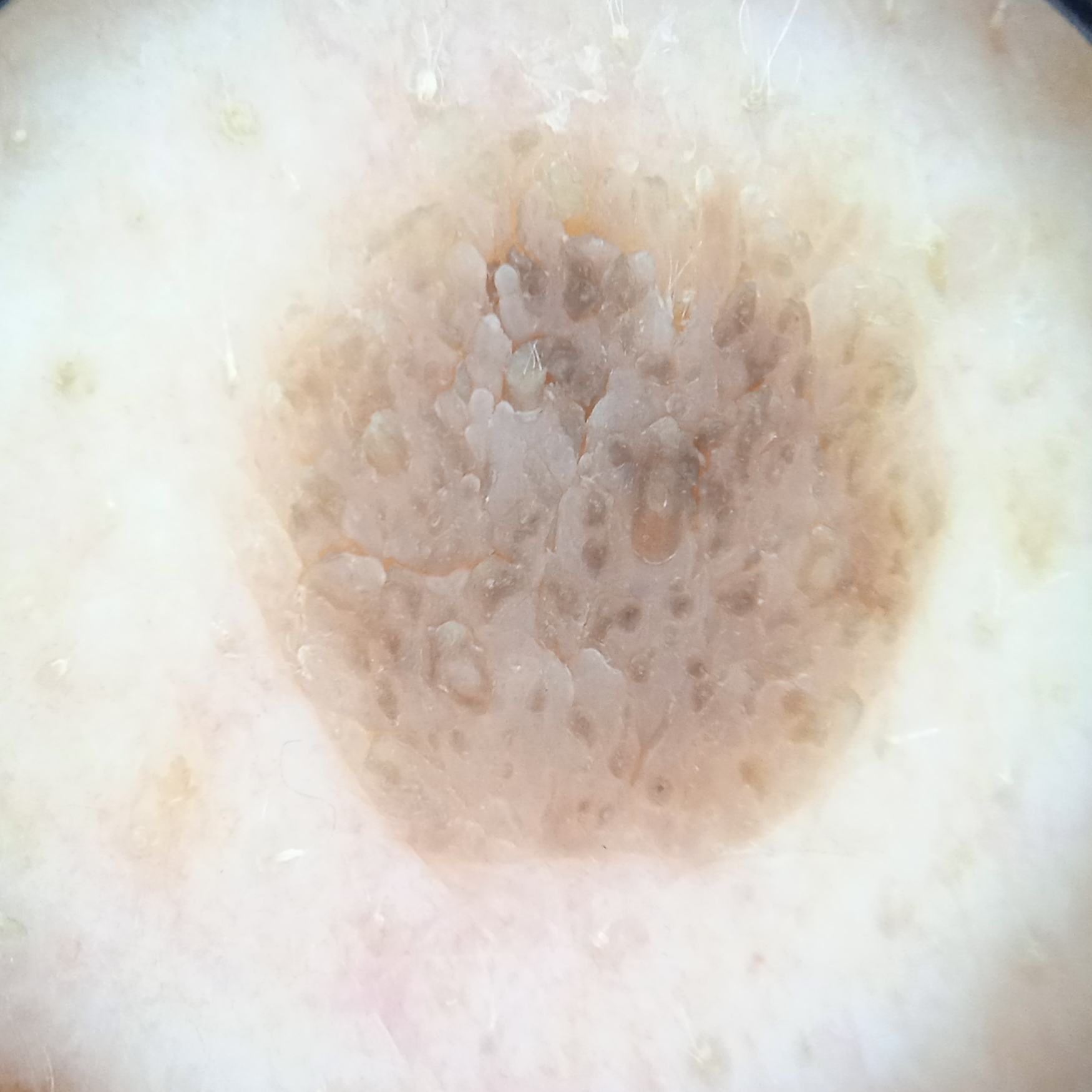assessment: seborrheic keratosis (dermatologist consensus)